A dermoscopic close-up of a skin lesion, the subject is a male about 15 years old — 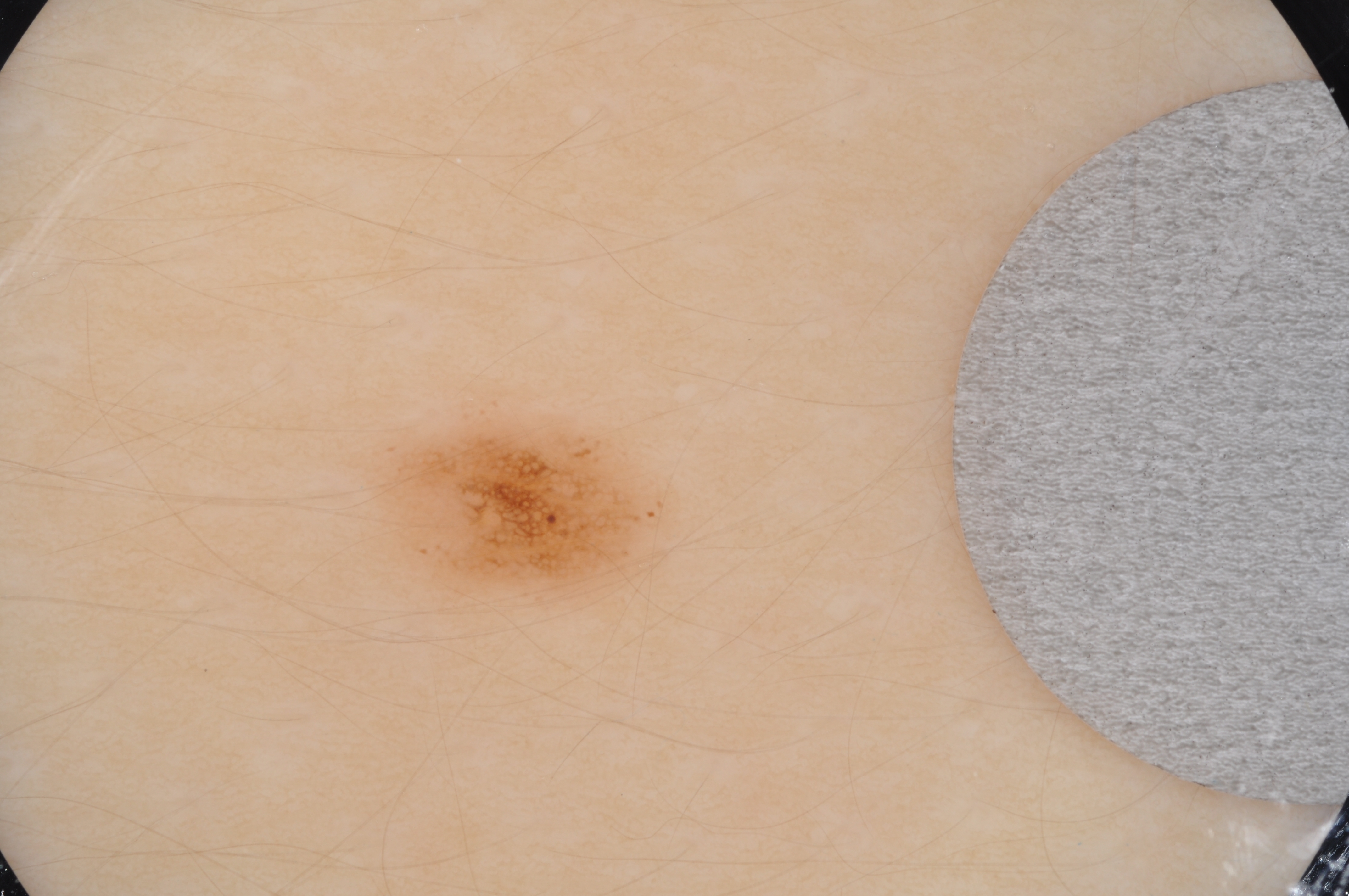dermoscopic_features:
  present:
    - pigment network
  absent:
    - globules
    - streaks
    - milia-like cysts
    - negative network
lesion_extent: small
lesion_location:
  bbox_xyxy:
    - 370
    - 402
    - 673
    - 617
diagnosis:
  name: melanocytic nevus
  malignancy: benign
  lineage: melanocytic
  provenance: clinical